Located on the leg · the subject is 50–59, female · close-up view · symptoms reported: enlargement and bothersome appearance:
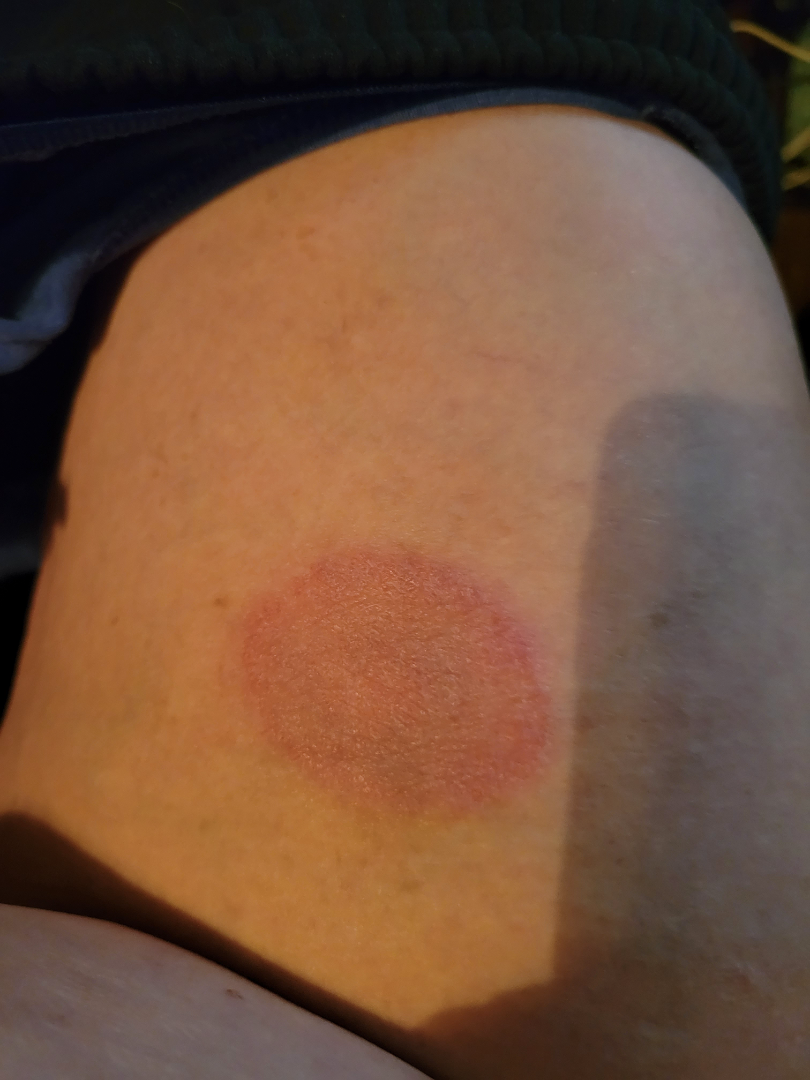On dermatologist assessment of the image, the favored diagnosis is Drug Rash.